A dermatoscopic image of a skin lesion.
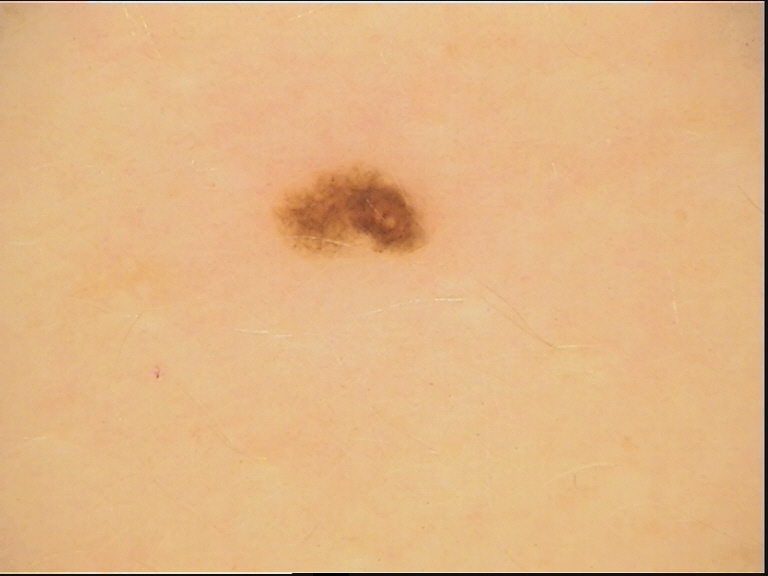label: dysplastic junctional nevus (expert consensus)